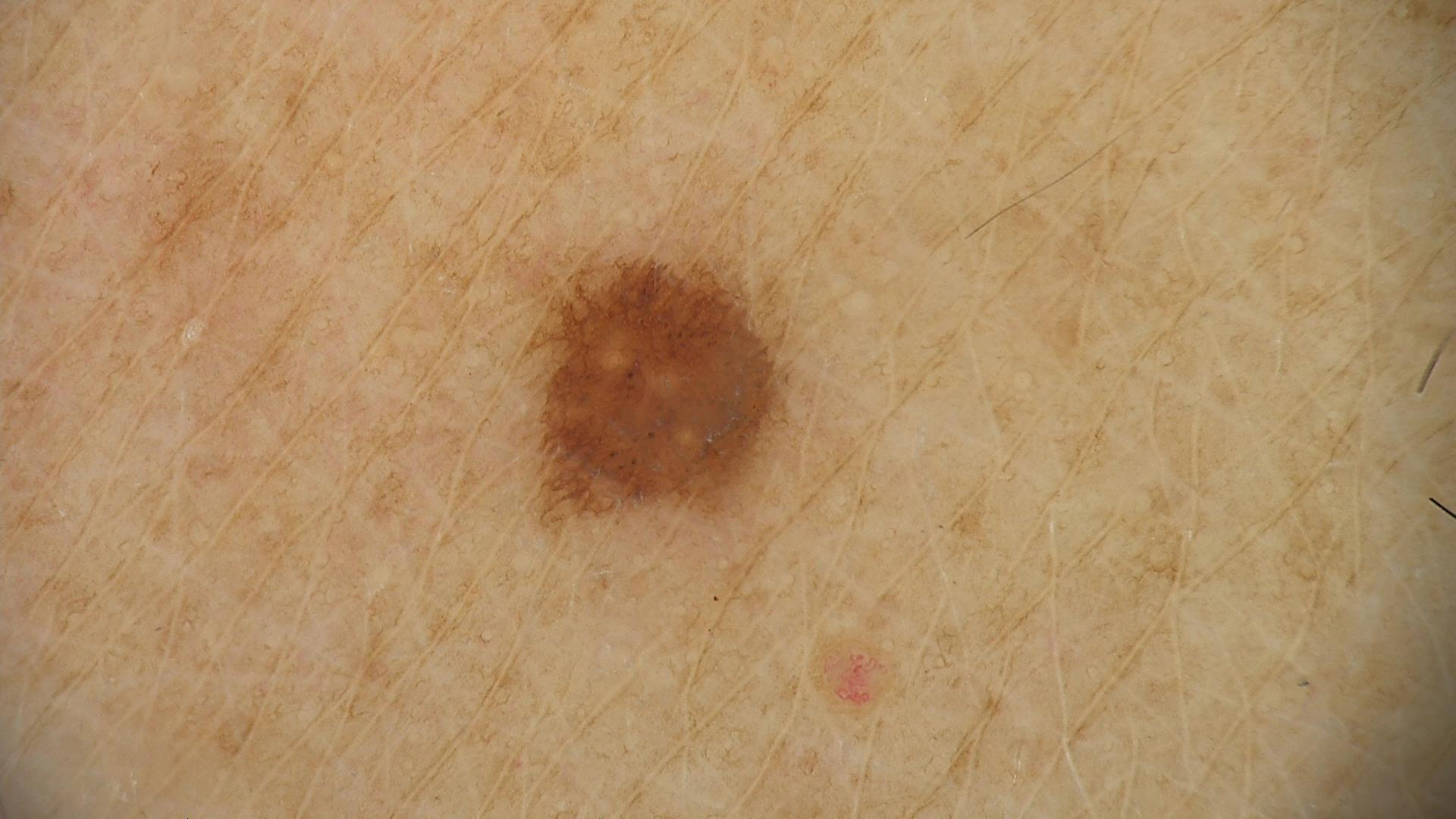Impression: Classified as a dysplastic junctional nevus.